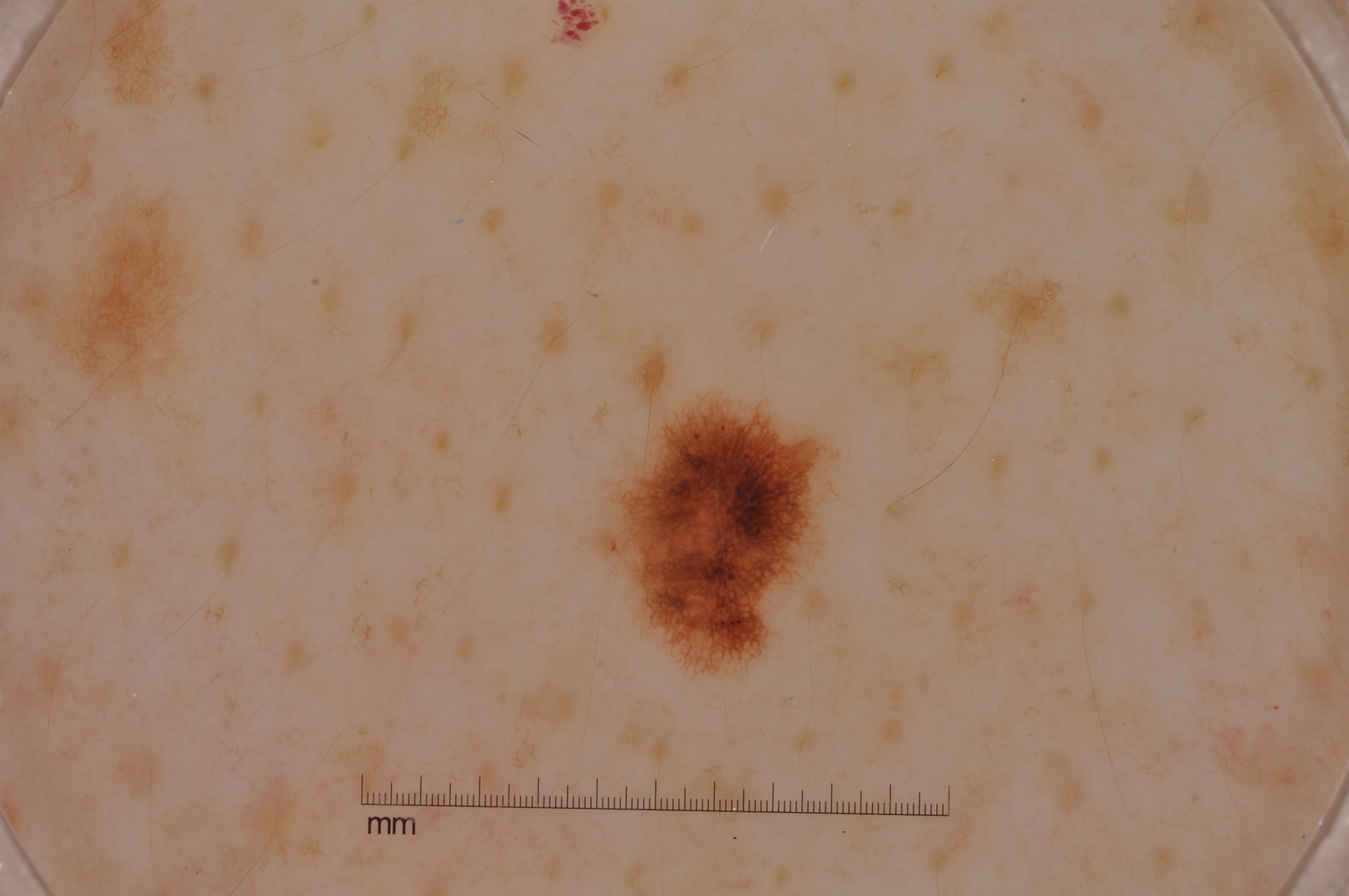imaging = dermoscopy
patient = female, in their mid- to late 40s
location = 611, 406, 822, 658
features = pigment network; absent: negative network, milia-like cysts, and streaks
size = ~3% of the field
diagnosis = a melanocytic nevus, a benign skin lesion